A clinical photograph showing a skin lesion. A female patient age 80. Fitzpatrick II: 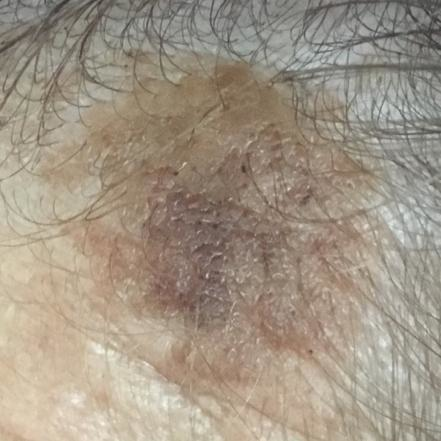Located on the face. The lesion measures 7 × 5 mm. Clinically diagnosed as a seborrheic keratosis.